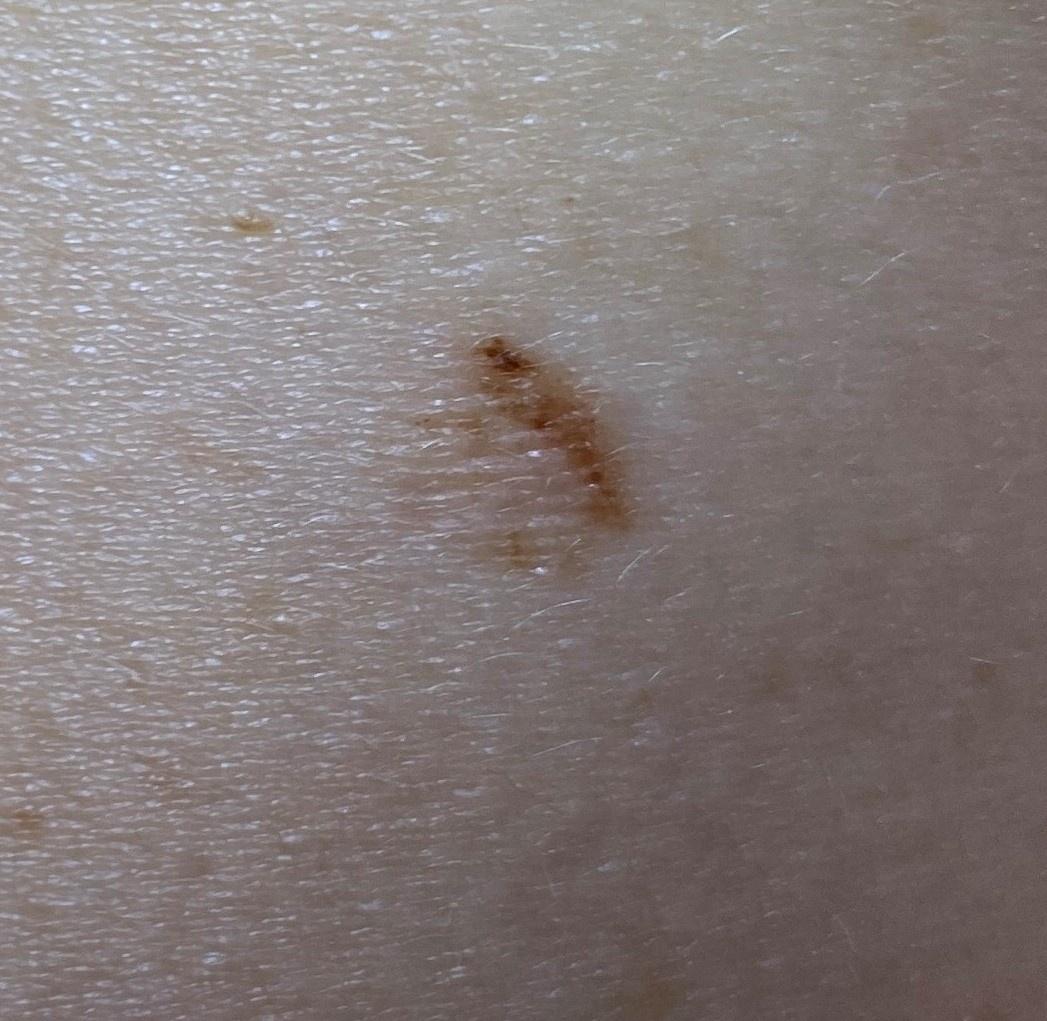<skin_lesion>
<skin_type>II</skin_type>
<patient>
<age_approx>20</age_approx>
<sex>female</sex>
</patient>
<melanoma_history>
<personal_hx_melanoma>false</personal_hx_melanoma>
<family_hx_melanoma>false</family_hx_melanoma>
</melanoma_history>
<image>clinical photo (overview)</image>
<lesion_location>
<region>the trunk</region>
<detail>the posterior trunk</detail>
</lesion_location>
<diagnosis>
<name>Nevus</name>
<malignancy>benign</malignancy>
<confirmation>histopathology</confirmation>
<lineage>melanocytic</lineage>
</diagnosis>
</skin_lesion>